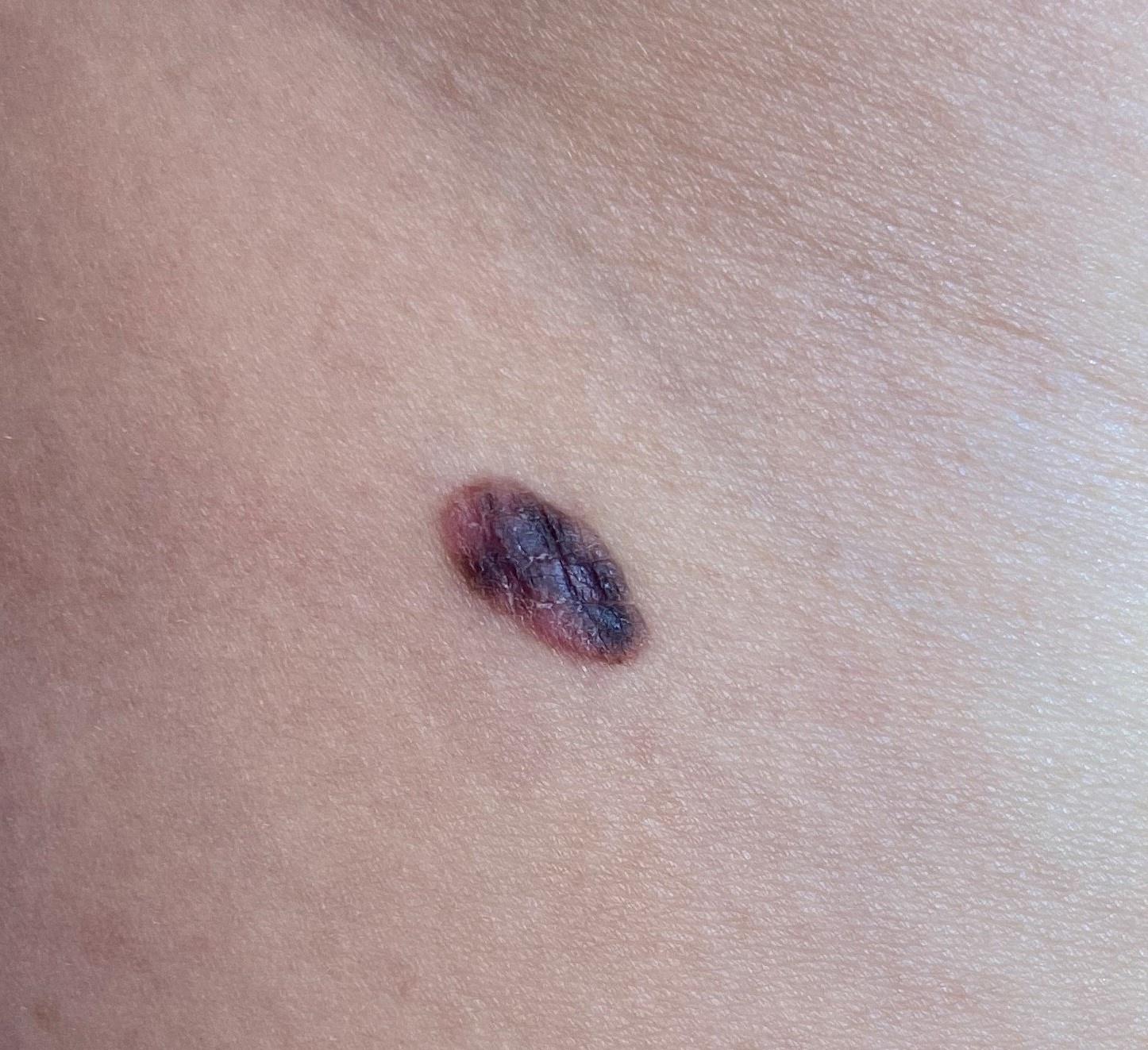melanoma history: a first-degree relative with melanoma
modality: clinical photograph
subject: female, aged around 30
location: a lower extremity
diagnostic label: Nevus (biopsy-proven)